A male patient, approximately 25 years of age; a dermatoscopic image of a skin lesion:
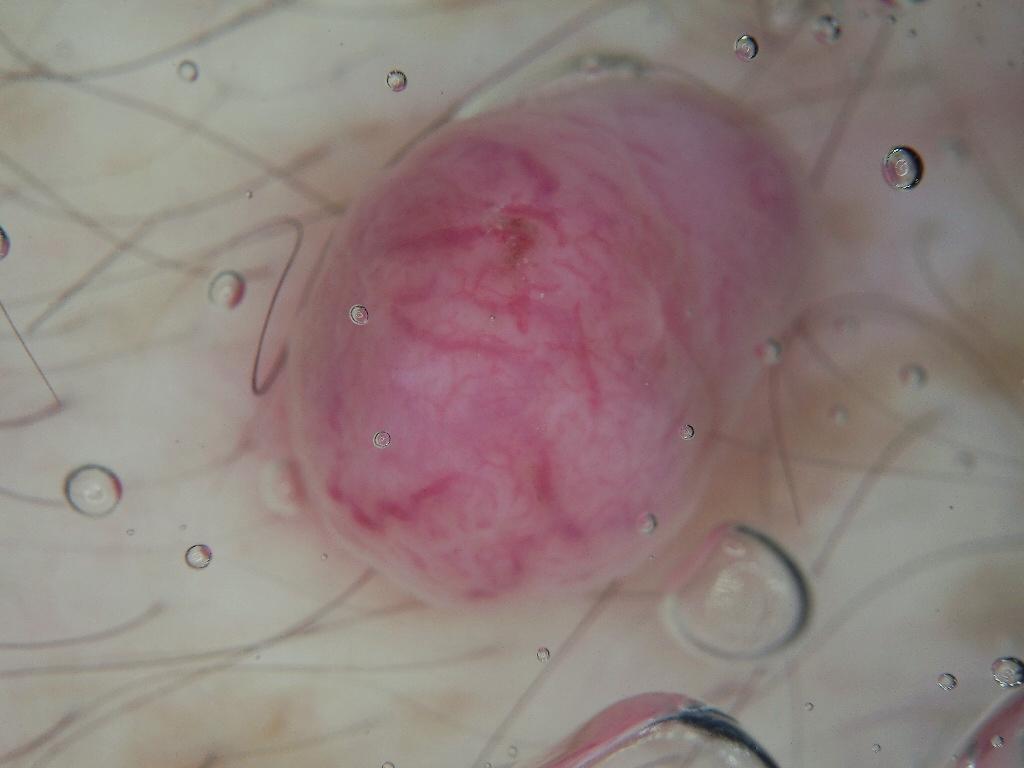{
  "dermoscopic_features": {
    "present": [],
    "absent": [
      "negative network",
      "pigment network",
      "milia-like cysts",
      "streaks"
    ]
  },
  "lesion_location": {
    "bbox_xyxy": [
      267,
      57,
      824,
      624
    ]
  },
  "diagnosis": {
    "name": "melanocytic nevus",
    "malignancy": "benign",
    "lineage": "melanocytic",
    "provenance": "clinical"
  }
}